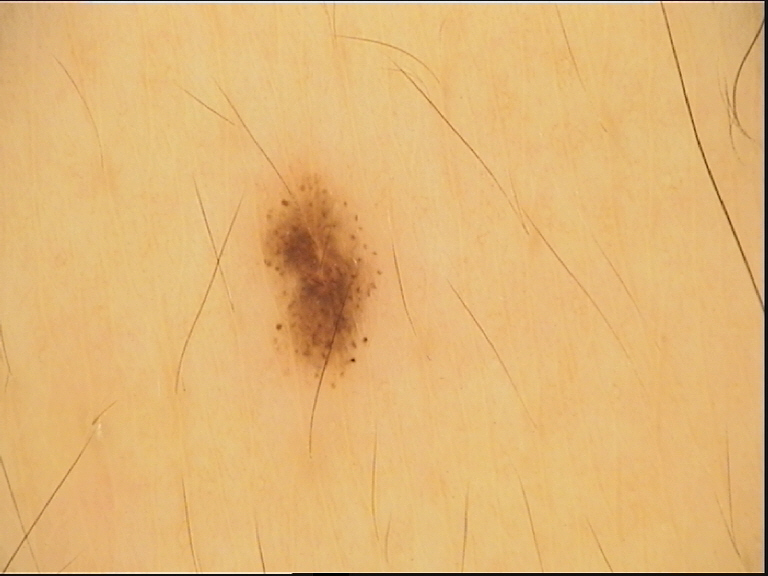Consistent with a dysplastic junctional nevus.